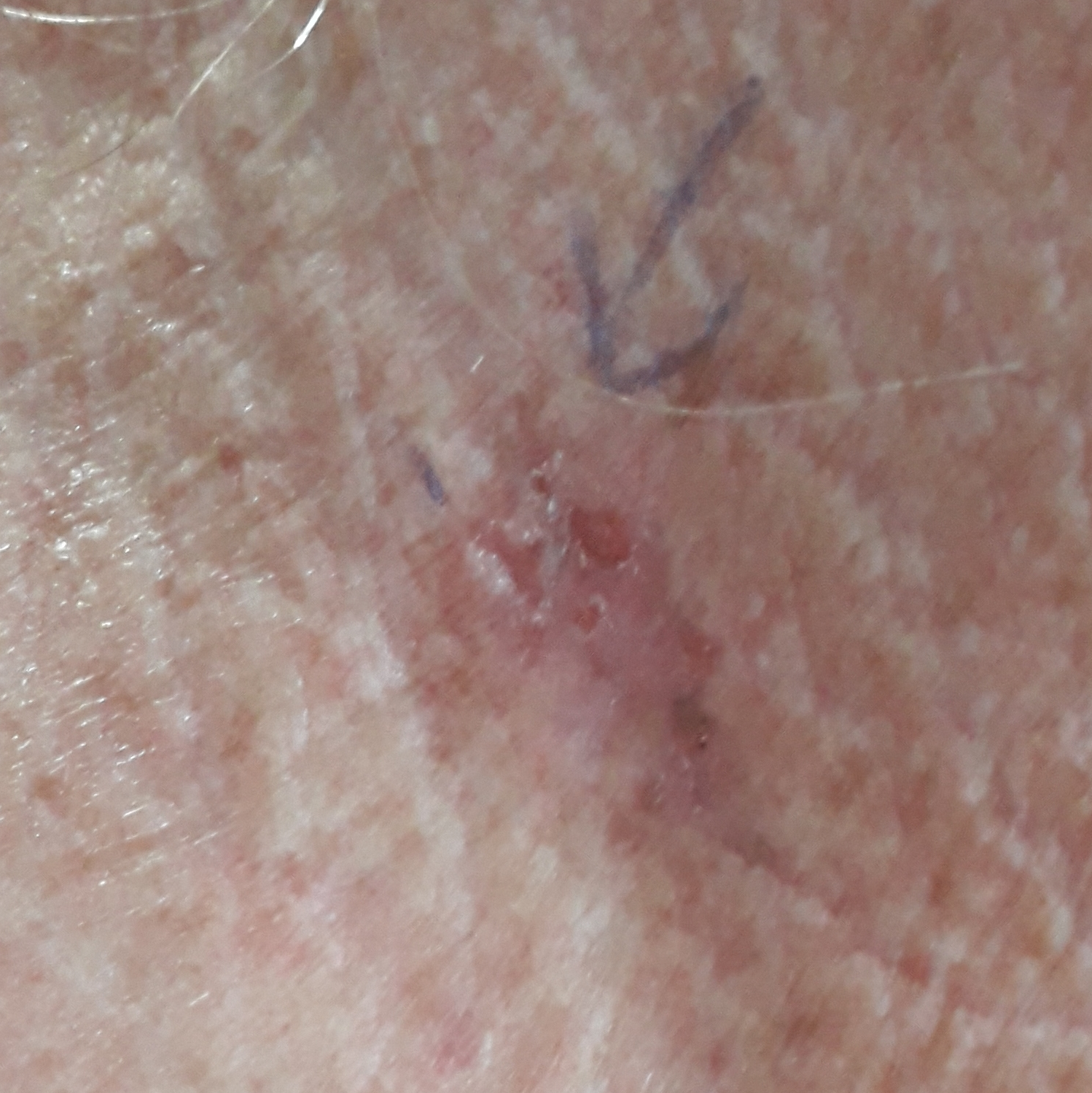Impression: Consistent with an actinic keratosis.